A clinical photograph showing a skin lesion in context · FST II · a male patient about 70 years old · the chart records a first-degree relative with melanoma:
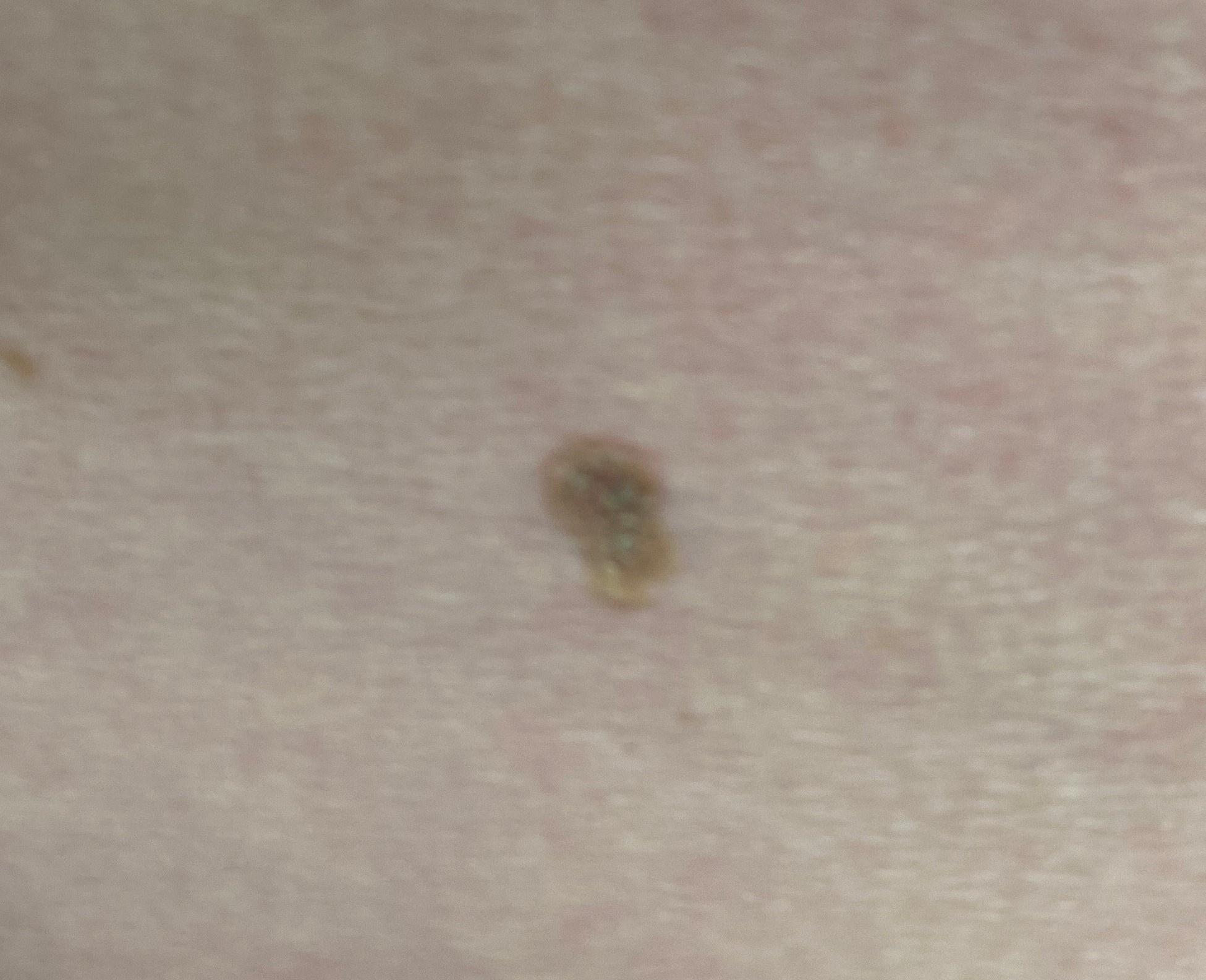<record>
  <lesion_location>
    <region>a lower extremity</region>
  </lesion_location>
  <diagnosis>
    <name>Seborrheic keratosis</name>
    <malignancy>benign</malignancy>
    <confirmation>expert clinical impression</confirmation>
    <lineage>epidermal</lineage>
  </diagnosis>
</record>